A contact-polarized dermoscopy image of a skin lesion; FST II: 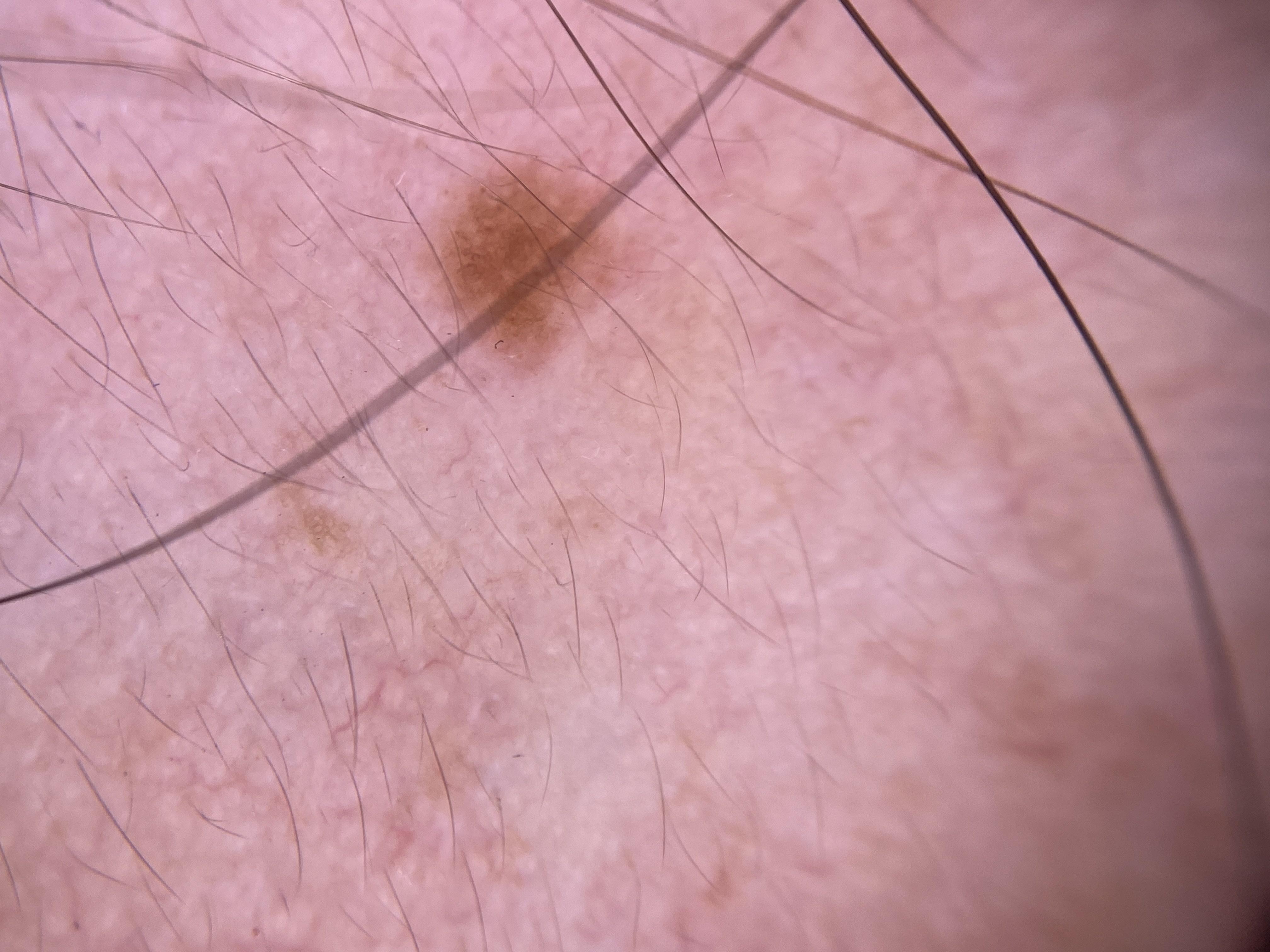Q: Where on the body is the lesion?
A: the head or neck
Q: What is this lesion?
A: Nevus